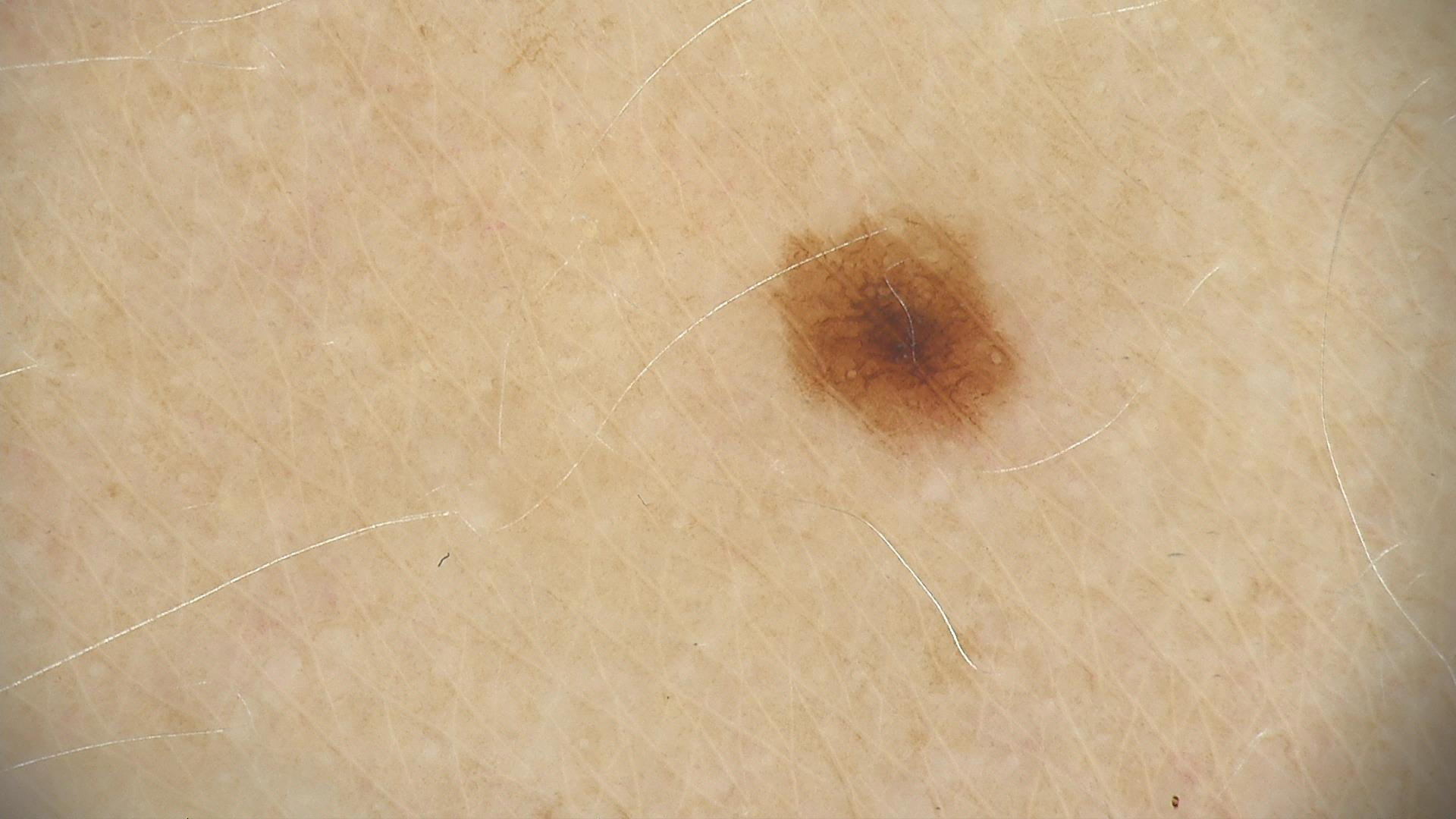A dermoscopic image of a skin lesion. Labeled as a dysplastic junctional nevus.